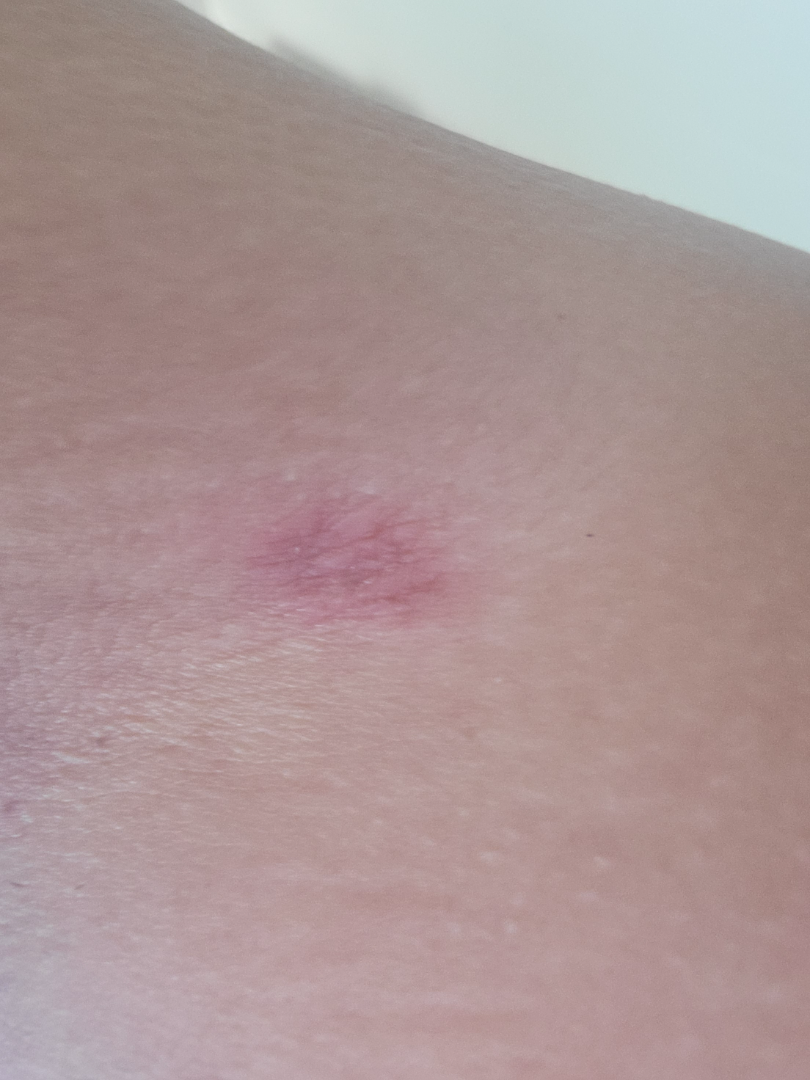Patient information:
This image was taken at a distance. The arm is involved.
Review:
Three dermatologists each reviewed the case: the primary impression is Hidradenitis; also raised was Abscess.